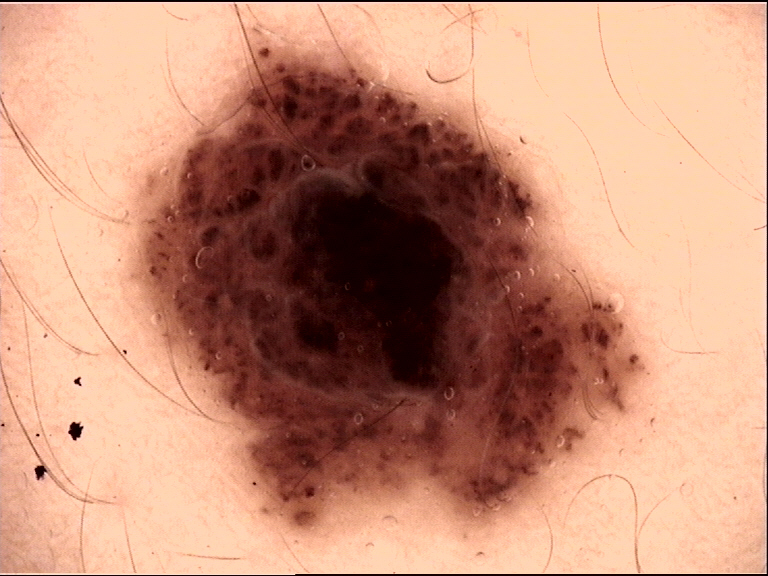The diagnosis was a compound nevus.